A dermoscopy image of a single skin lesion — 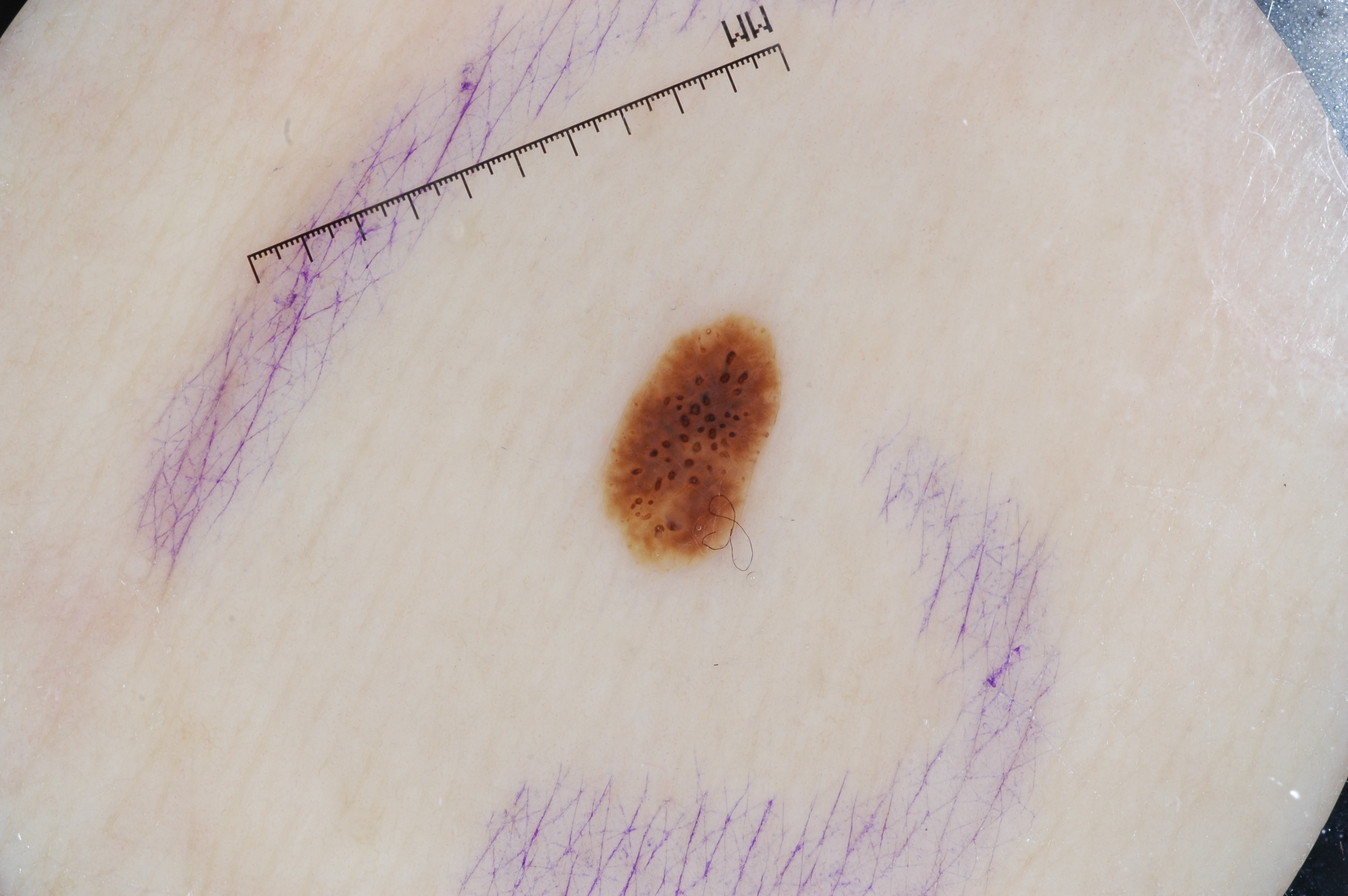<case>
<dermoscopic_features>
  <present>milia-like cysts</present>
  <absent>pigment network, negative network, streaks</absent>
</dermoscopic_features>
<lesion_location>
  <bbox_xyxy>611, 322, 779, 560</bbox_xyxy>
</lesion_location>
<diagnosis>
  <name>seborrheic keratosis</name>
  <malignancy>benign</malignancy>
  <lineage>keratinocytic</lineage>
  <provenance>clinical</provenance>
</diagnosis>
</case>